Dermoscopy of a skin lesion, the subject is a female roughly 45 years of age:
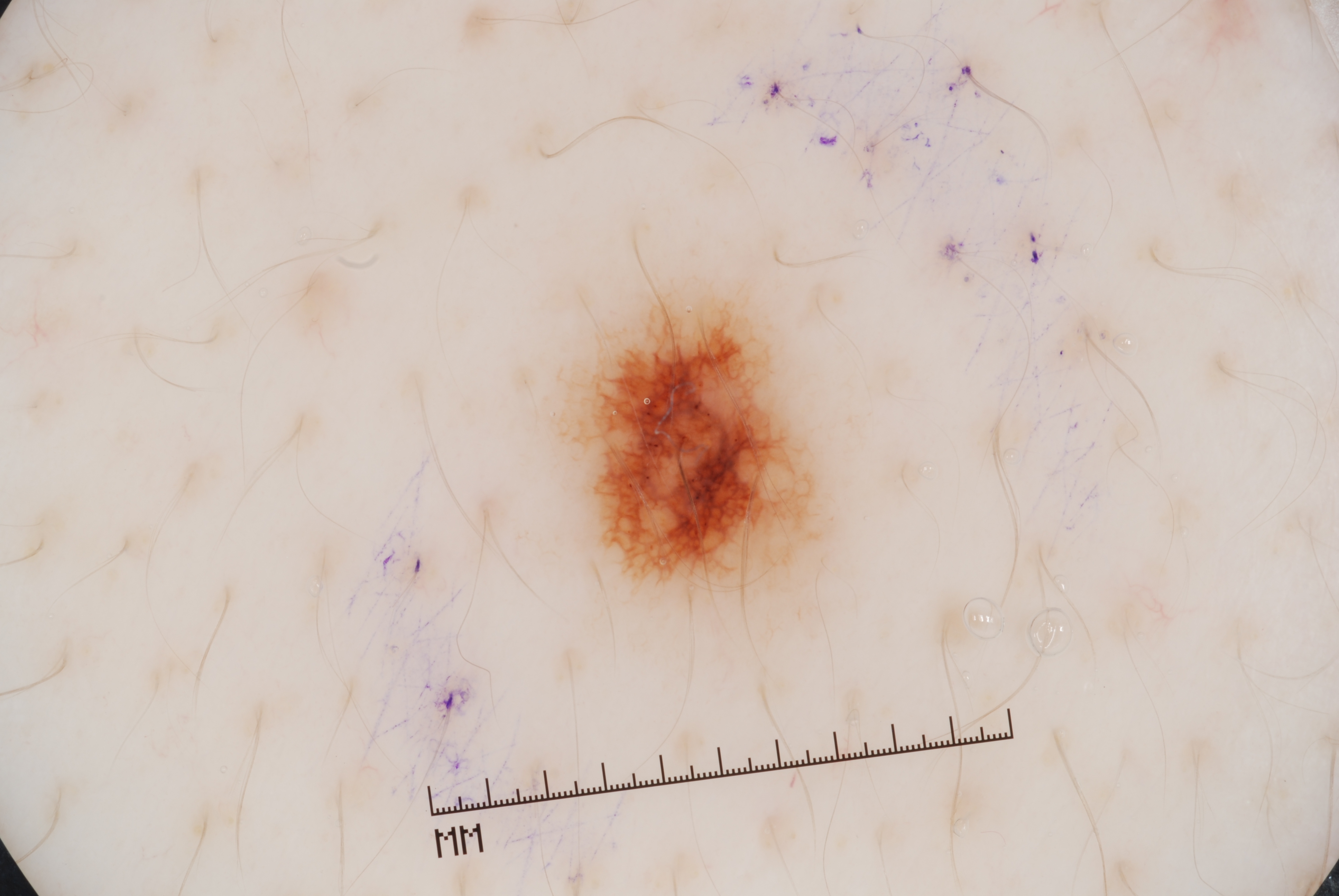{"lesion_location": {"bbox_xyxy": [565, 287, 826, 609]}, "dermoscopic_features": {"present": ["pigment network"], "absent": ["streaks", "milia-like cysts", "negative network"]}, "diagnosis": {"name": "melanocytic nevus", "malignancy": "benign", "lineage": "melanocytic", "provenance": "clinical"}}